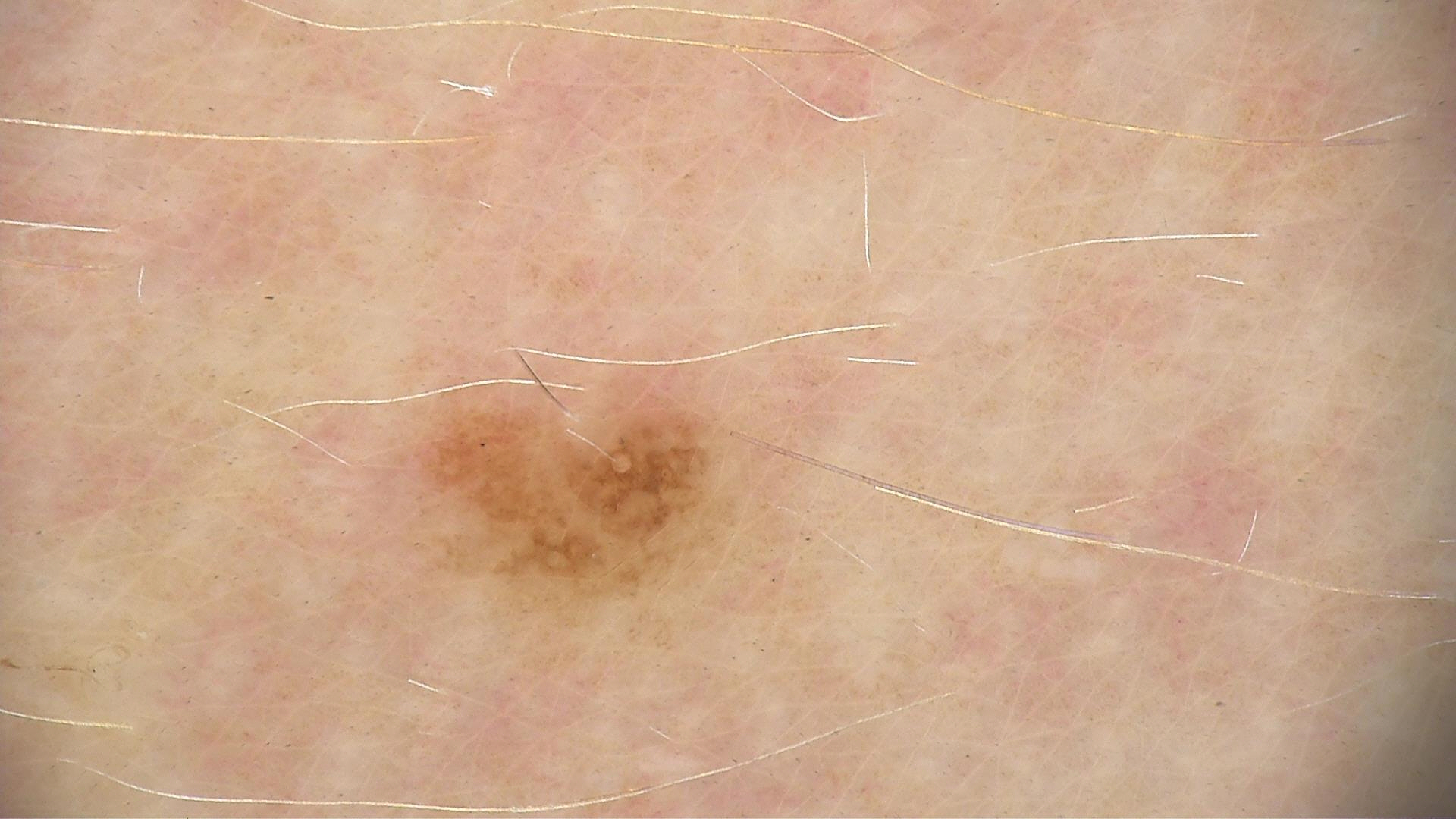<lesion>
<image>dermatoscopy</image>
<diagnosis>
<name>dysplastic junctional nevus</name>
<code>jd</code>
<malignancy>benign</malignancy>
<super_class>melanocytic</super_class>
<confirmation>expert consensus</confirmation>
</diagnosis>
</lesion>